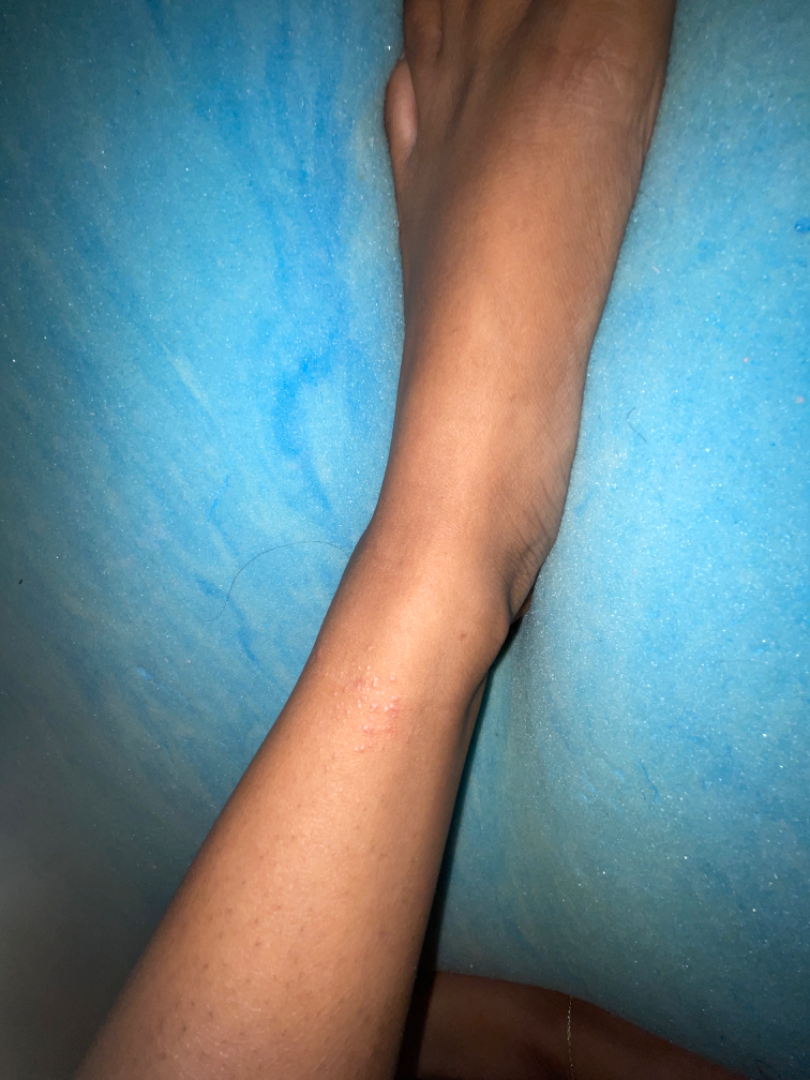No relevant systemic symptoms.
The contributor notes itching.
The contributor notes the condition has been present for one to three months.
An image taken at a distance.
The patient described the issue as a rash.
The contributor notes the lesion is raised or bumpy.
The leg is involved.
Favoring Eczema; also on the differential is Lichen planus/lichenoid eruption; less likely is Lichen nitidus; a remote consideration is Allergic Contact Dermatitis; less probable is Lichen spinulosus.